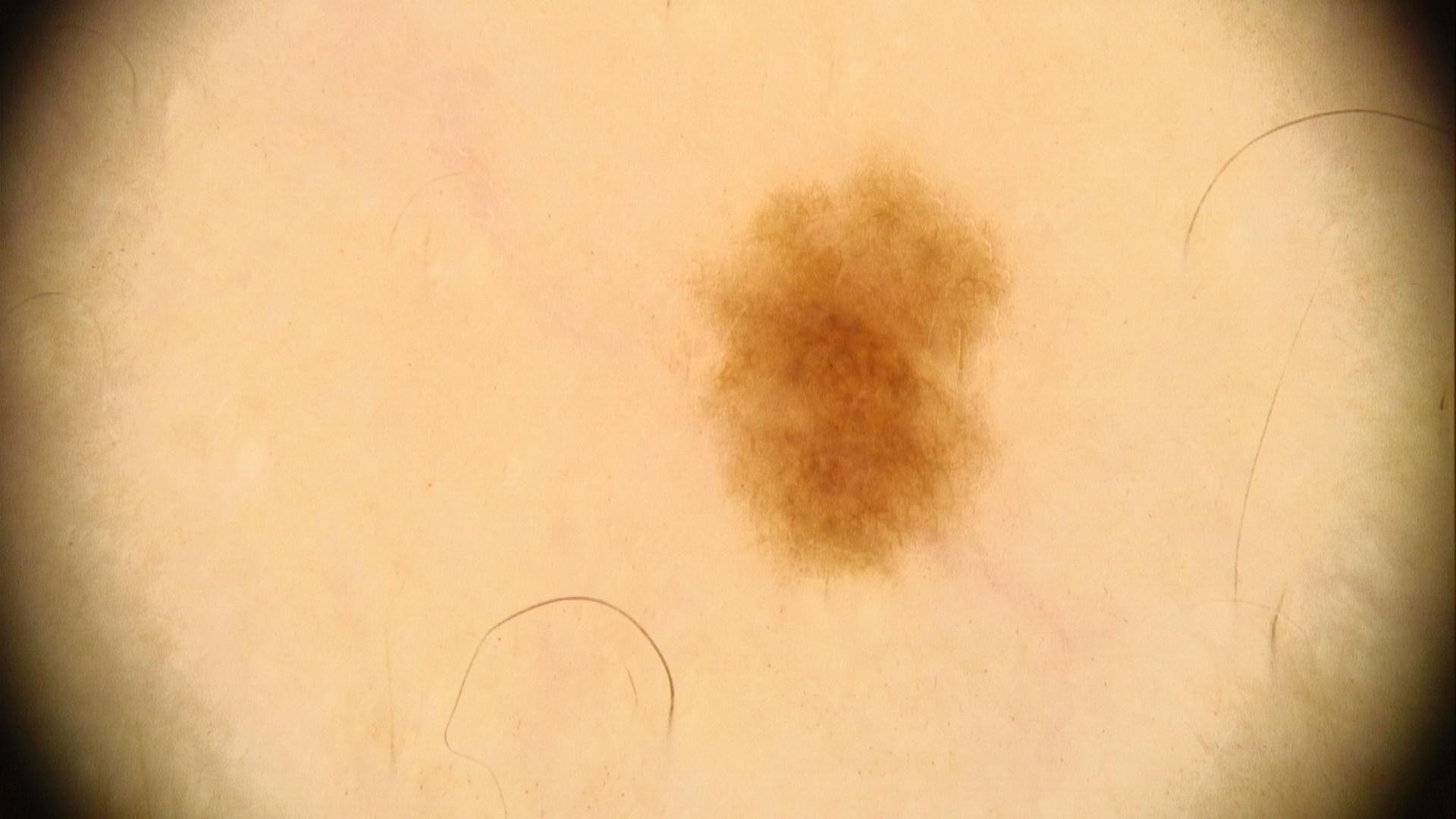skin_type: IV
patient:
  age_approx: 55
  sex: female
melanoma_history:
  personal_hx_melanoma: false
  family_hx_melanoma: false
lesion_location:
  region: a lower extremity
diagnosis:
  name: Nevus
  malignancy: benign
  confirmation: expert clinical impression
  lineage: melanocytic